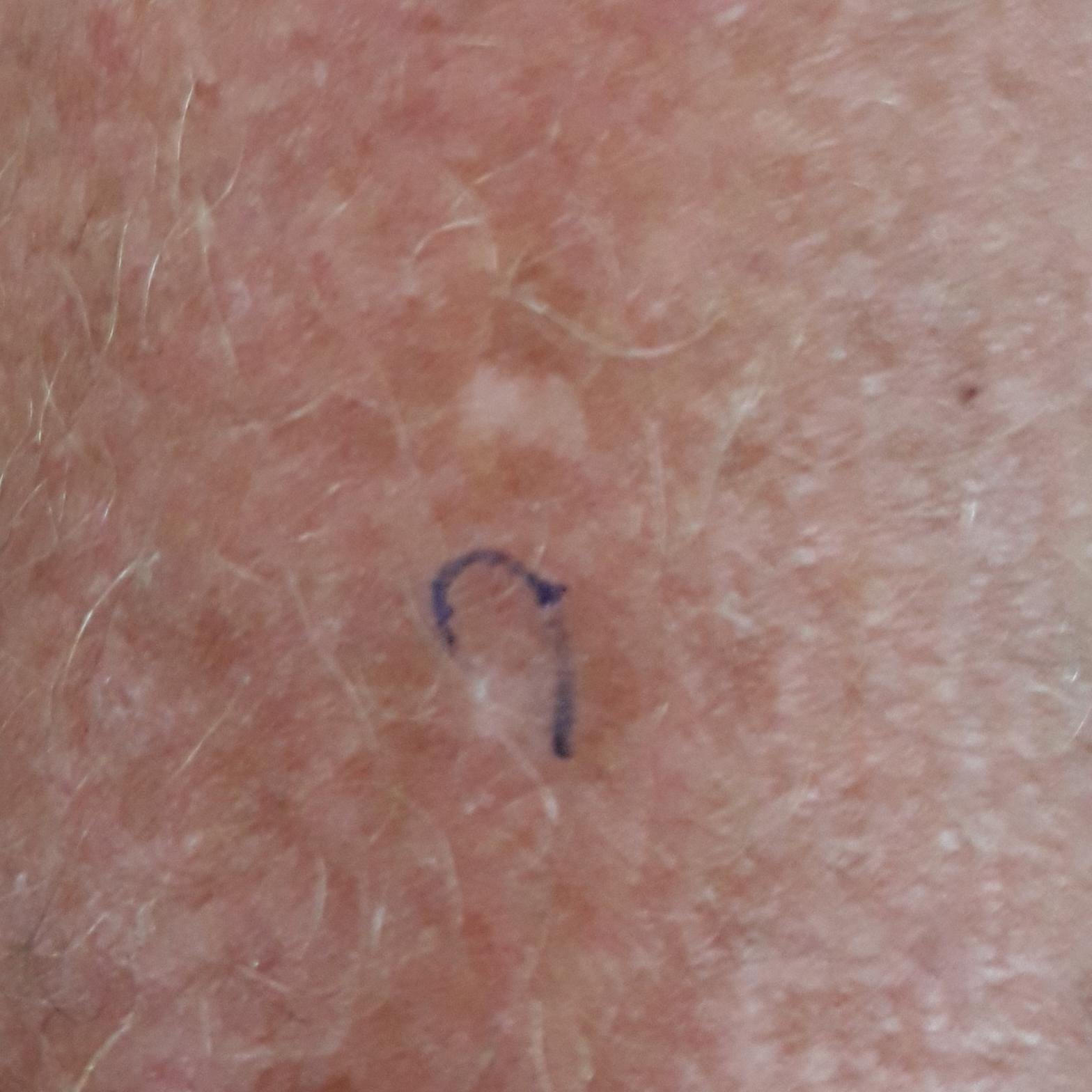Q: What is this lesion?
A: actinic keratosis (clinical consensus)